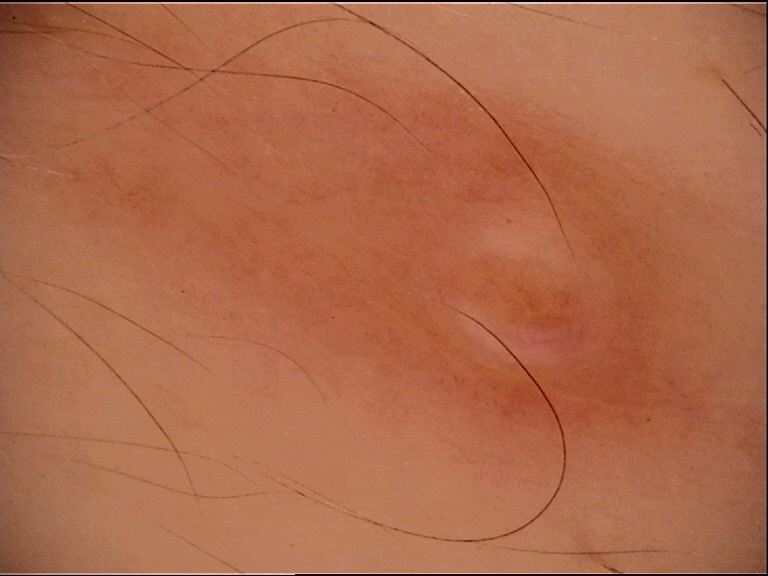Q: What was the diagnostic impression?
A: dermal nevus (expert consensus)